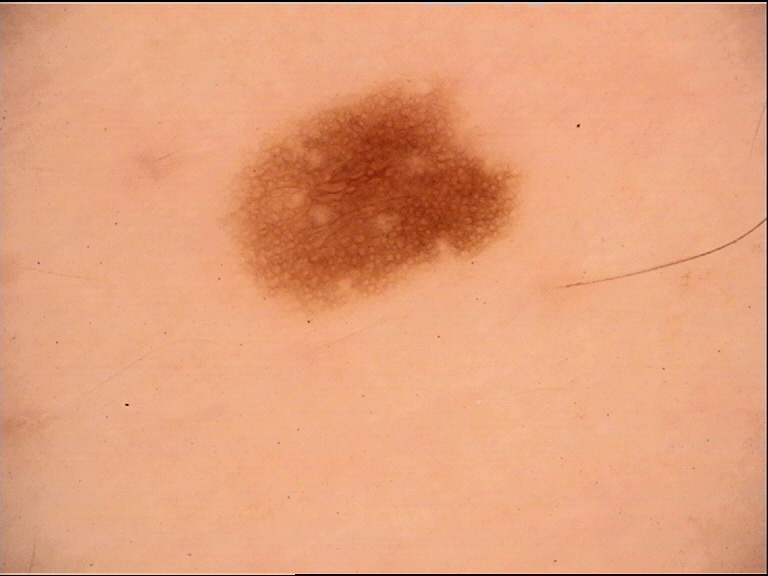<dermoscopy>
  <image>dermoscopy</image>
  <diagnosis>
    <name>dysplastic junctional nevus</name>
    <code>jd</code>
    <malignancy>benign</malignancy>
    <super_class>melanocytic</super_class>
    <confirmation>expert consensus</confirmation>
  </diagnosis>
</dermoscopy>